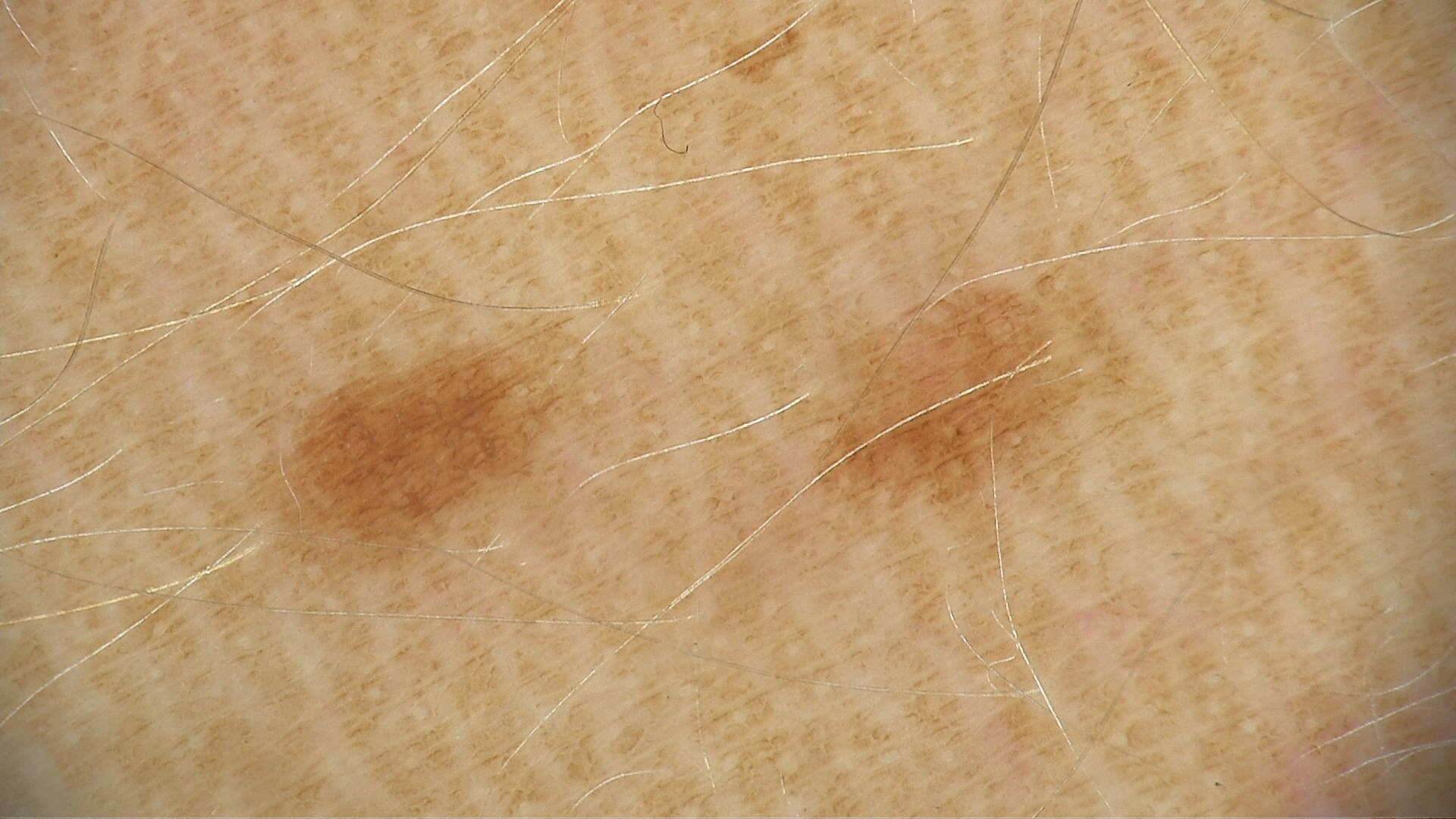{
  "diagnosis": {
    "name": "dysplastic junctional nevus",
    "code": "jd",
    "malignancy": "benign",
    "super_class": "melanocytic",
    "confirmation": "expert consensus"
  }
}